The affected area is the arm · female contributor, age 50–59 · this image was taken at an angle.
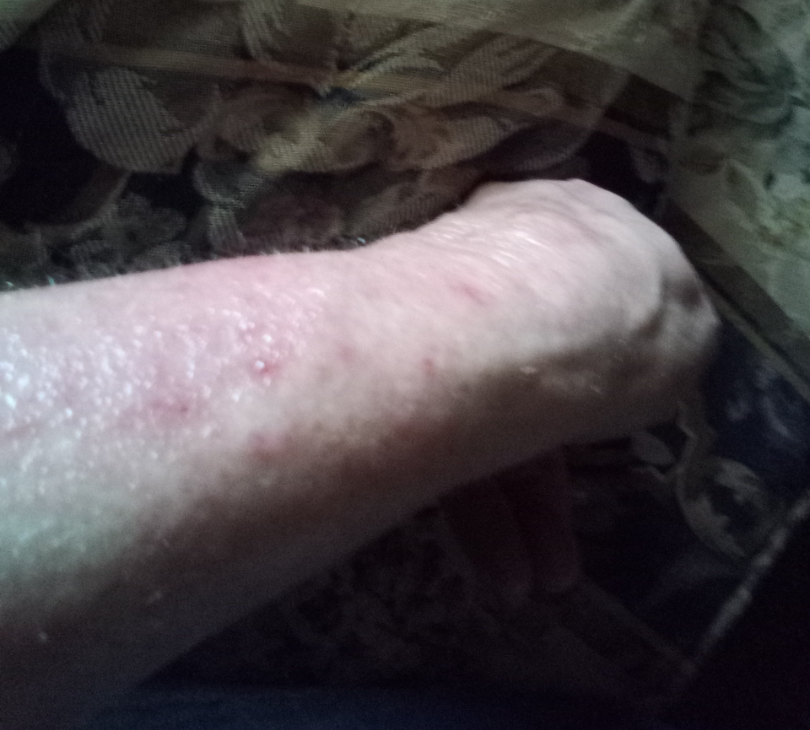Findings:
* assessment — not assessable